A skin lesion imaged with a dermatoscope: 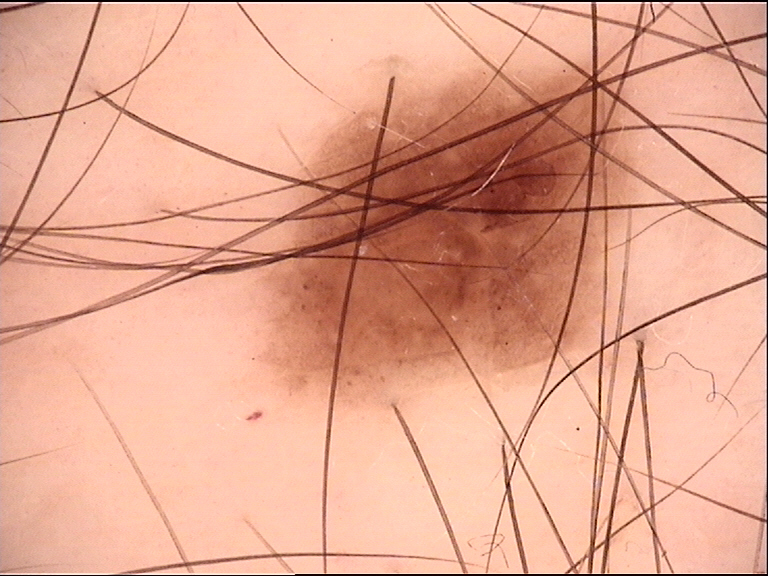diagnostic label: dysplastic junctional nevus (expert consensus)